The photograph is a close-up of the affected area; texture is reported as raised or bumpy.
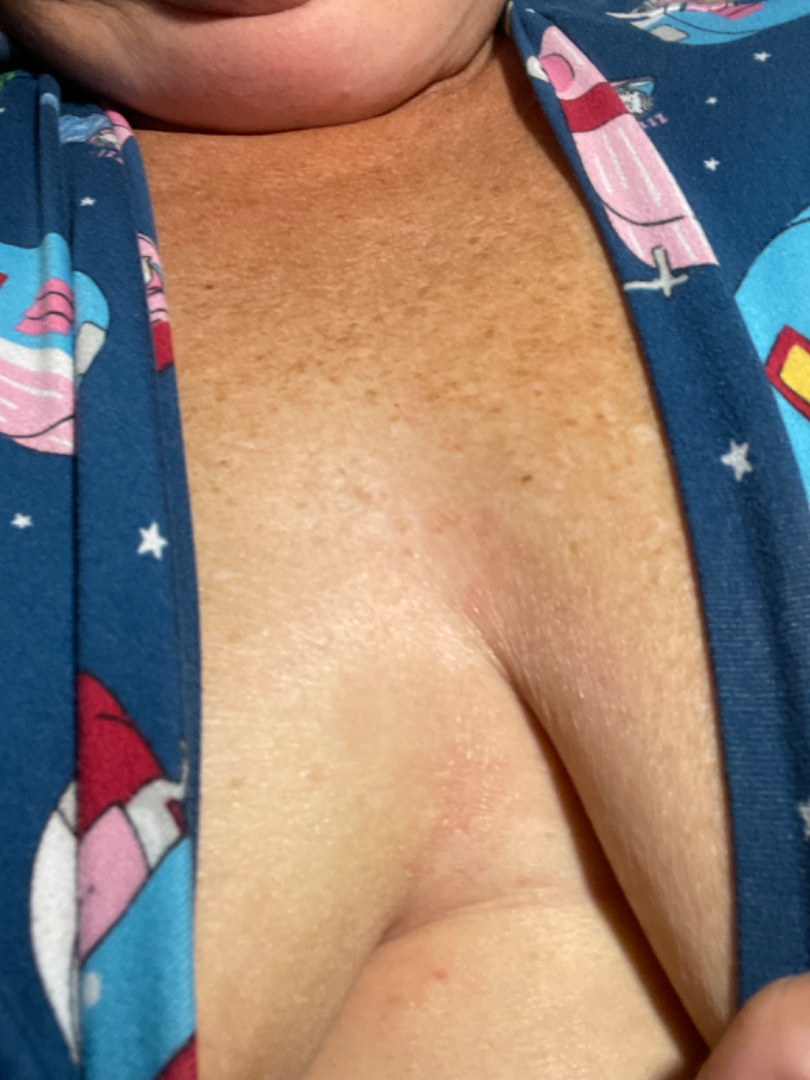The image was not sufficient for the reviewer to characterize the skin condition.